This is a close-up image: 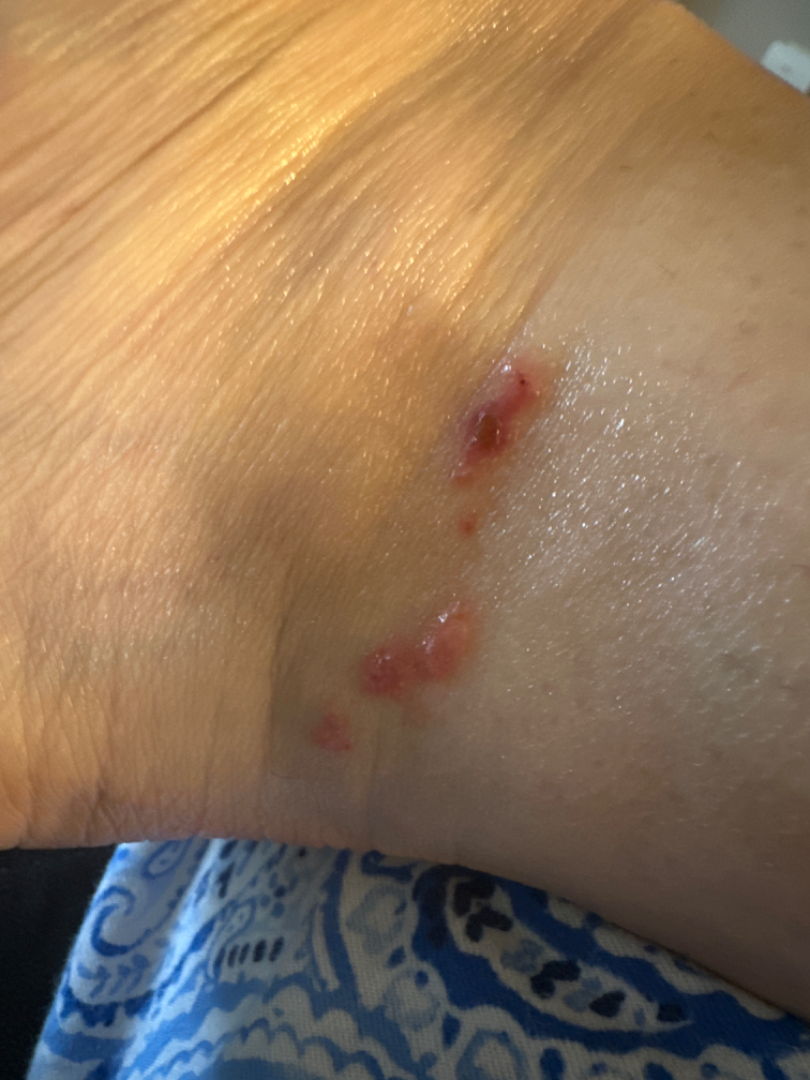Assessment:
The reviewer was unable to grade this case for skin condition.